The subject is a female aged 30–39; the lesion is associated with pain, burning, enlargement and itching; the photograph is a close-up of the affected area; the lesion involves the head or neck; the condition has been present for three to twelve months: 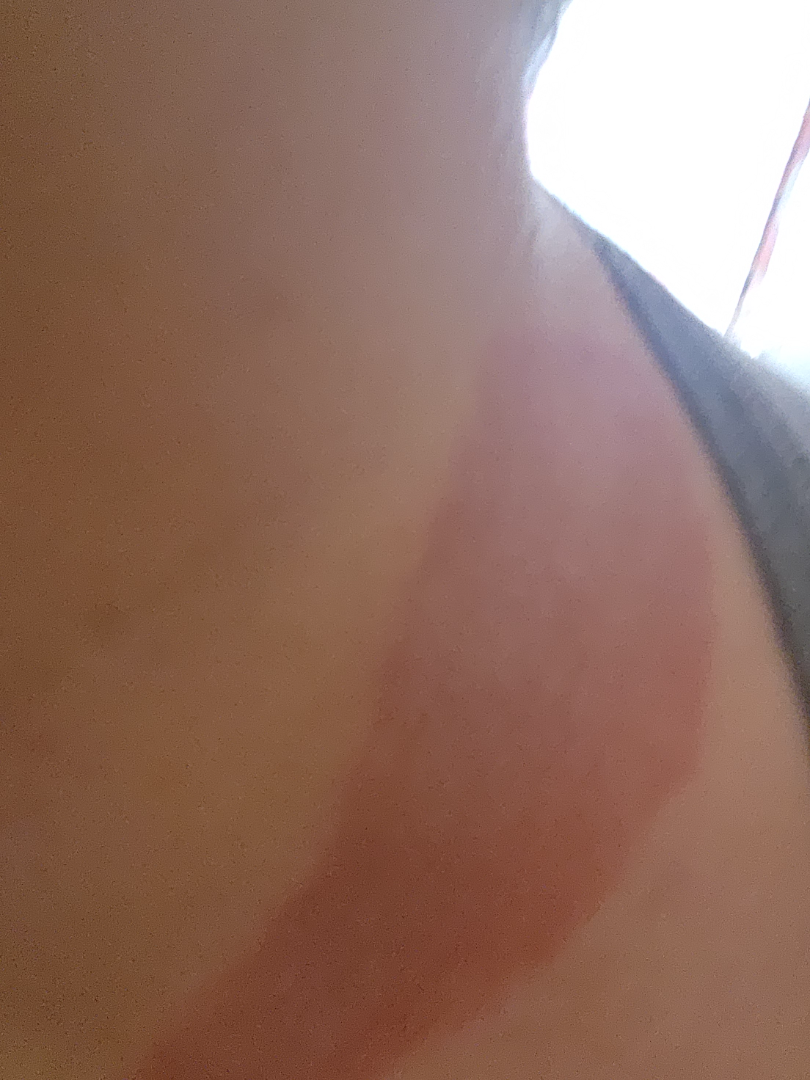differential = single-reviewer assessment: Psoriasis, Burn erythema of neck and Allergic Contact Dermatitis were each considered, in no particular order.